A male patient aged 68 — 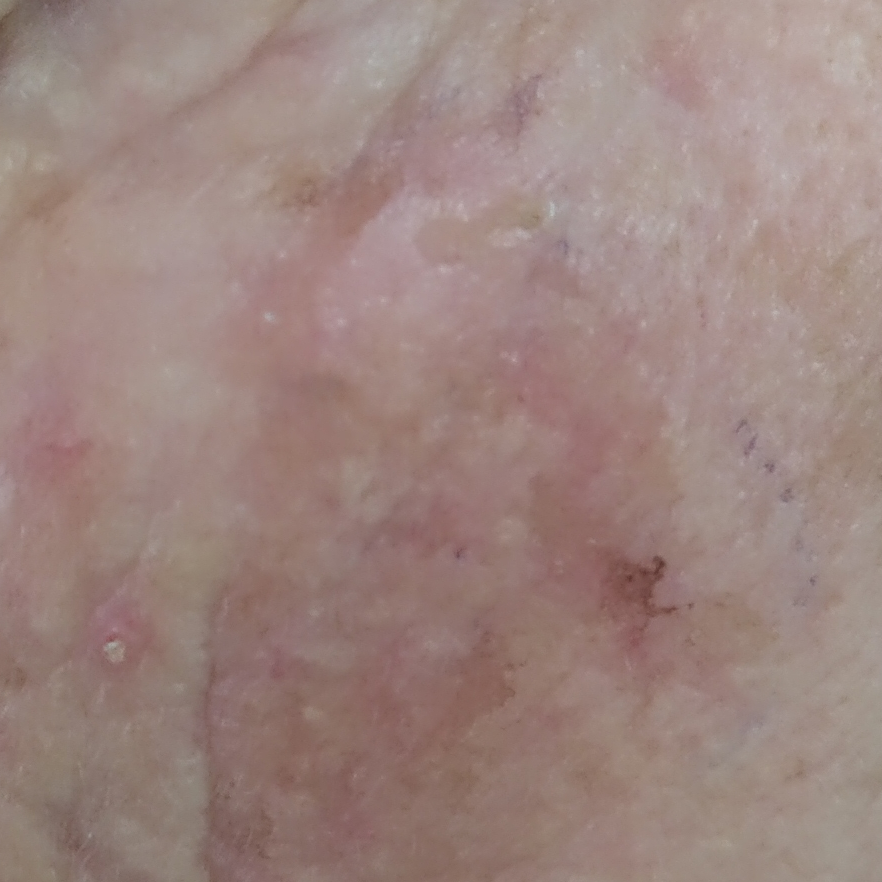<skin_lesion>
<diagnosis>
<name>actinic keratosis</name>
<code>ACK</code>
<malignancy>indeterminate</malignancy>
<confirmation>histopathology</confirmation>
</diagnosis>
</skin_lesion>